The affected area is the arm, leg and back of the hand · close-up view · the subject is a female aged 18–29 — 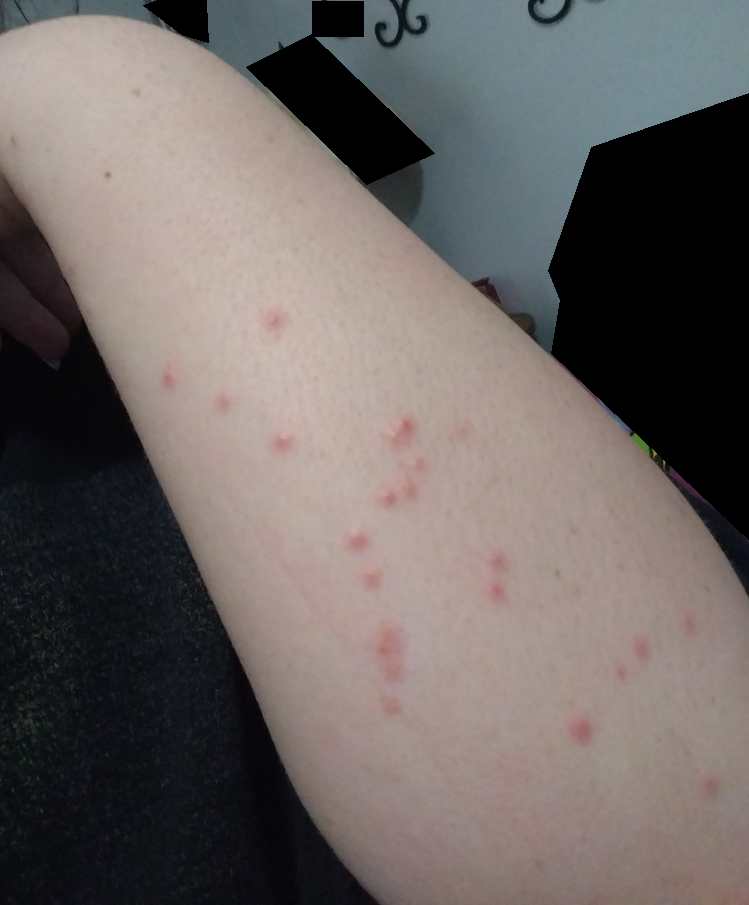{
  "differential": "Insect Bite"
}